A dermatoscopic image of a skin lesion. The patient is a female in their 80s: 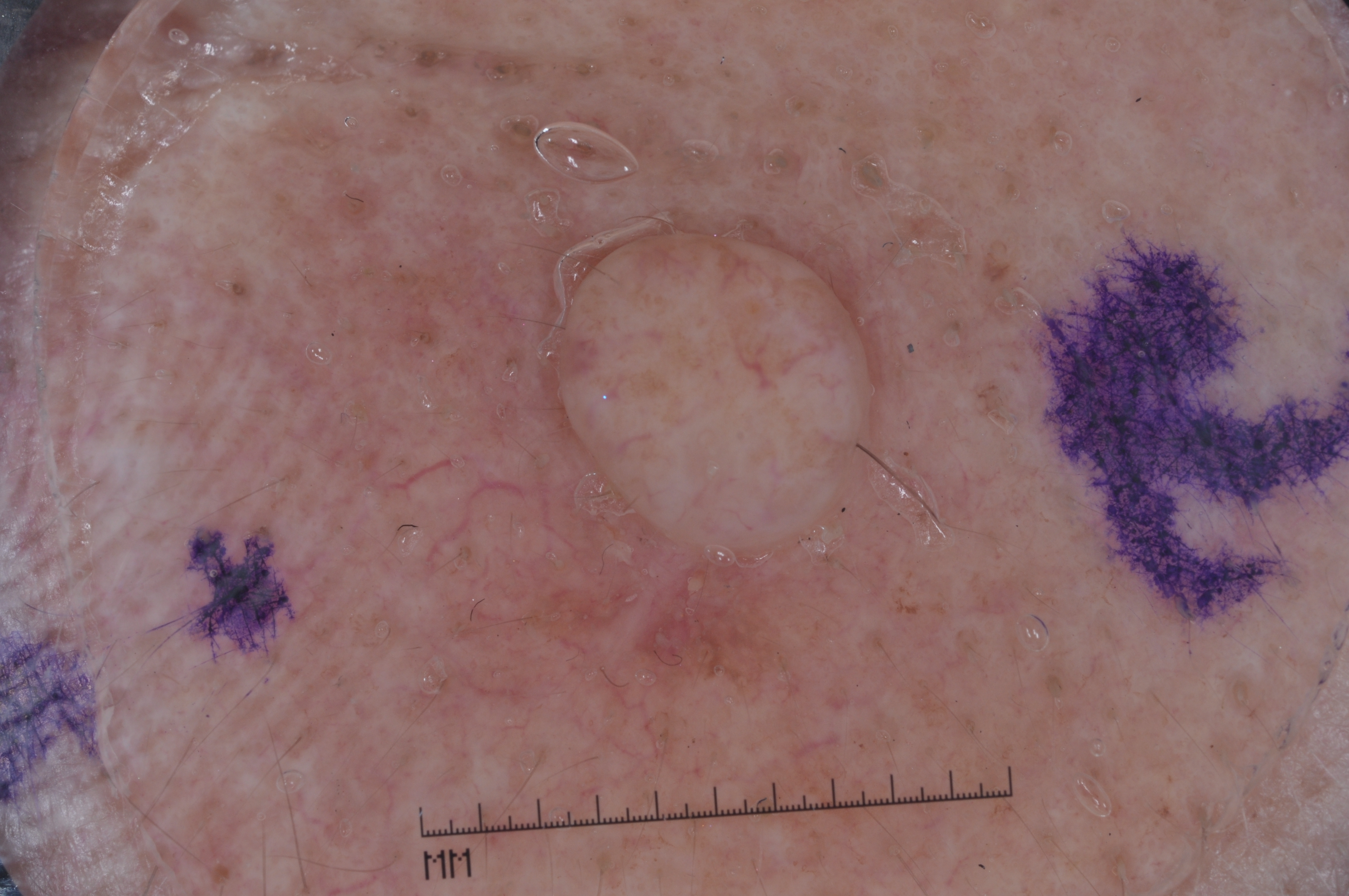Dermoscopy demonstrates no streaks, negative network, milia-like cysts, or pigment network. In (x1, y1, x2, y2) order, the visible lesion spans [546, 217, 885, 569]. Expert review diagnosed this as a melanocytic nevus, a benign lesion.